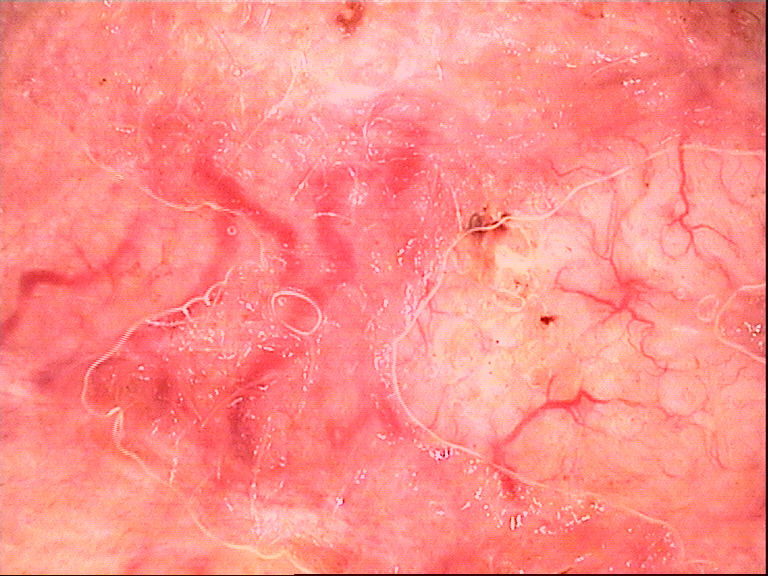Biopsy-confirmed as a basal cell carcinoma.